Few moles overall by the patient's own estimate. The patient says their skin reddens with sun exposure. A macroscopic clinical photograph of a skin lesion. A female subject age 71.
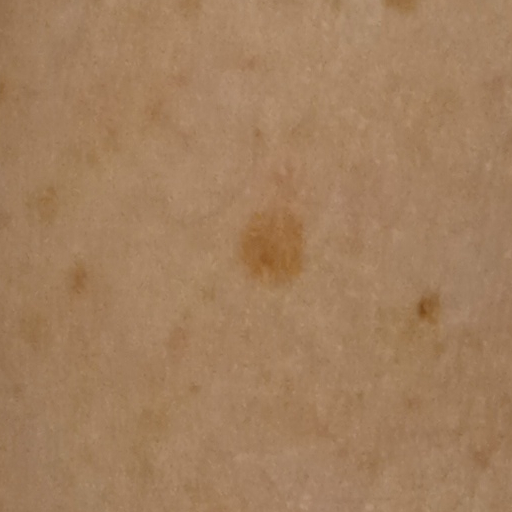Case:
• diagnostic label · melanocytic nevus (dermatologist consensus)